A female patient 75 years of age; Fitzpatrick skin type III; a clinical photo of a skin lesion taken with a smartphone; by history, pesticide exposure, prior malignancy (patient or family), and prior skin cancer (patient or family).
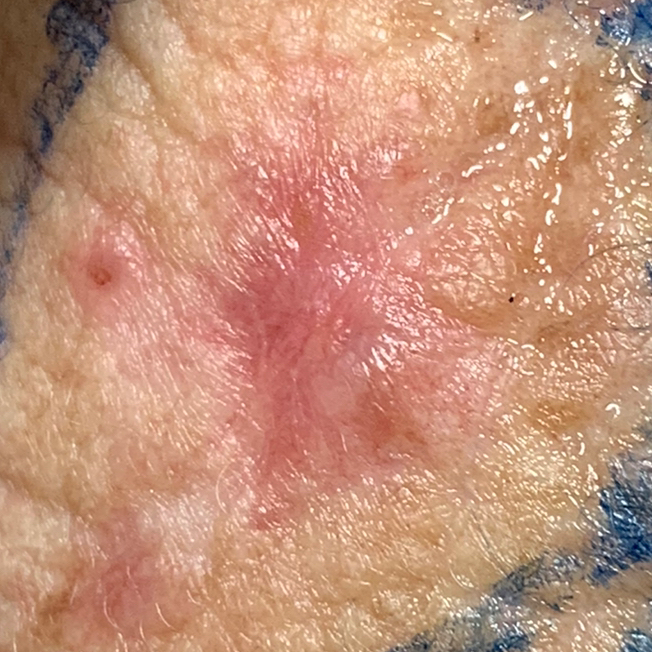anatomic site: the neck
diameter: 25 × 13 mm
symptoms: pain, growth / no bleeding
pathology: basal cell carcinoma (biopsy-proven)